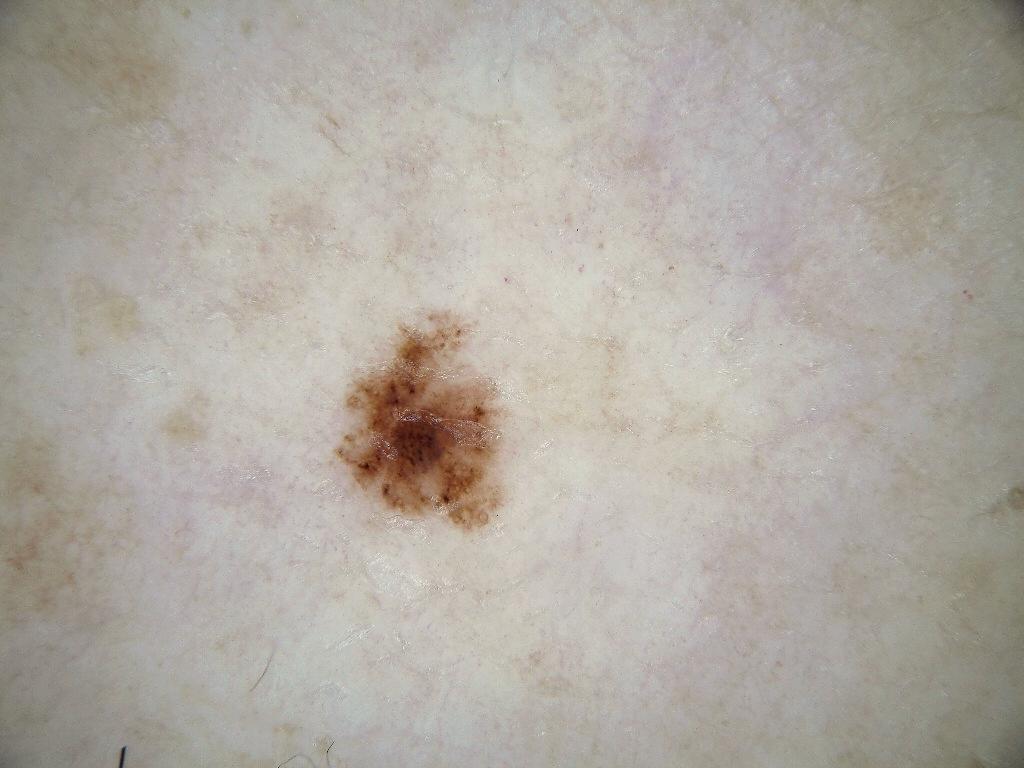modality = dermatoscopic image of a skin lesion; size = small; lesion location = 328 311 506 532; dermoscopic features assessed but absent = streaks and globules; diagnostic label = a benign lesion.